By self-report, a personal history of skin cancer and a personal history of cancer. The patient says their skin reddens with sun exposure. The patient describes having few moles overall. Dermoscopy of a skin lesion — 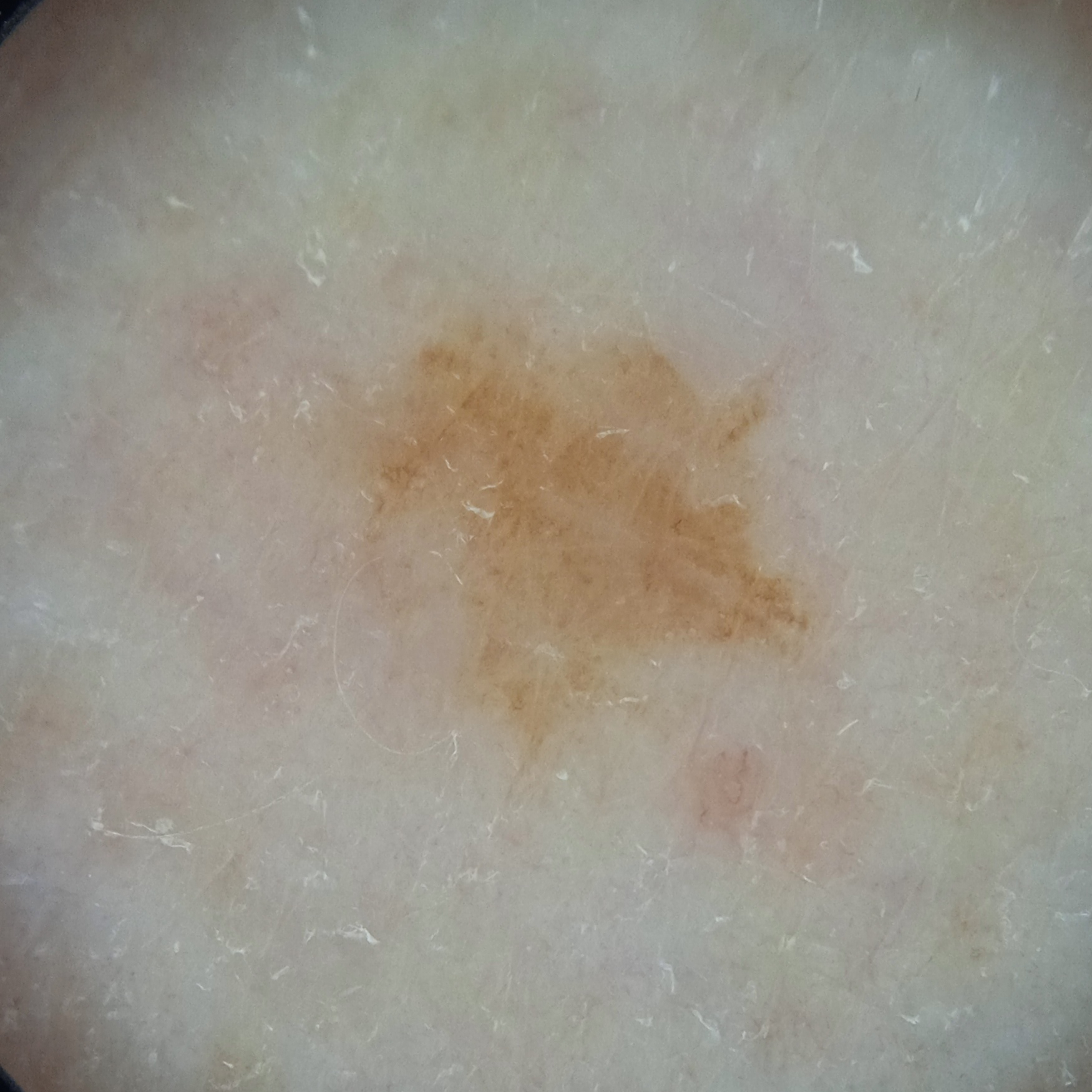Findings:
* anatomic site — an arm
* size — 6.1 mm
* assessment — melanocytic nevus (dermatologist consensus)